The condition has been present for less than one week. A close-up photograph. The lesion is associated with bothersome appearance and pain. The lesion is described as fluid-filled. The patient reported no systemic symptoms:
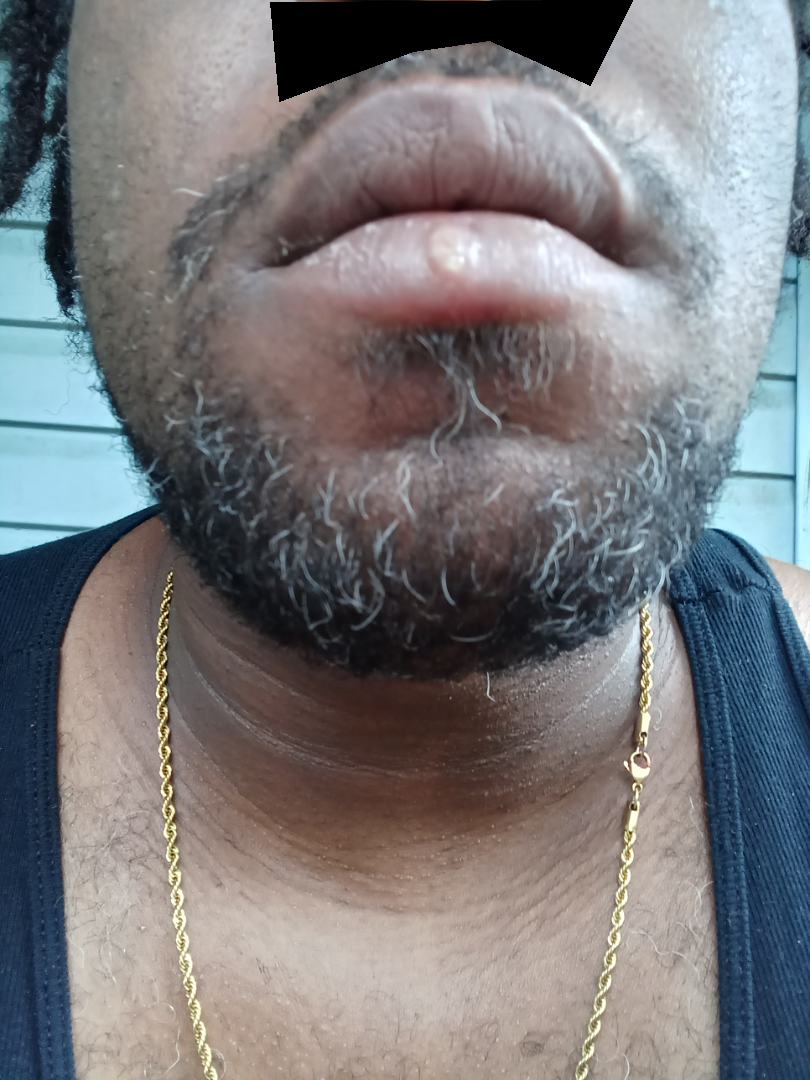Q: What was the assessment?
A: no findings on review